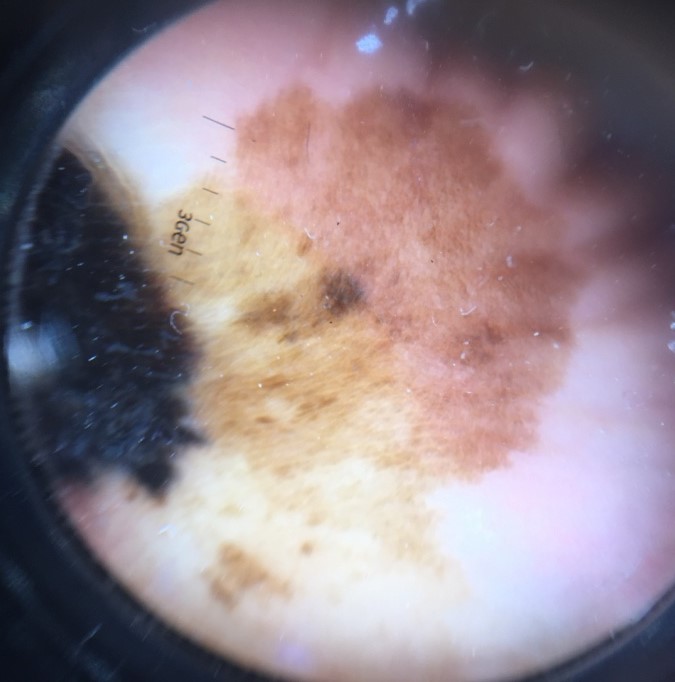{"diagnosis": {"name": "acral lentiginous melanoma", "code": "alm", "malignancy": "malignant", "super_class": "melanocytic", "confirmation": "histopathology"}}